A smartphone photograph of a skin lesion; a male patient aged 61; by history, prior skin cancer (patient or family); the patient was assessed as Fitzpatrick phototype III: 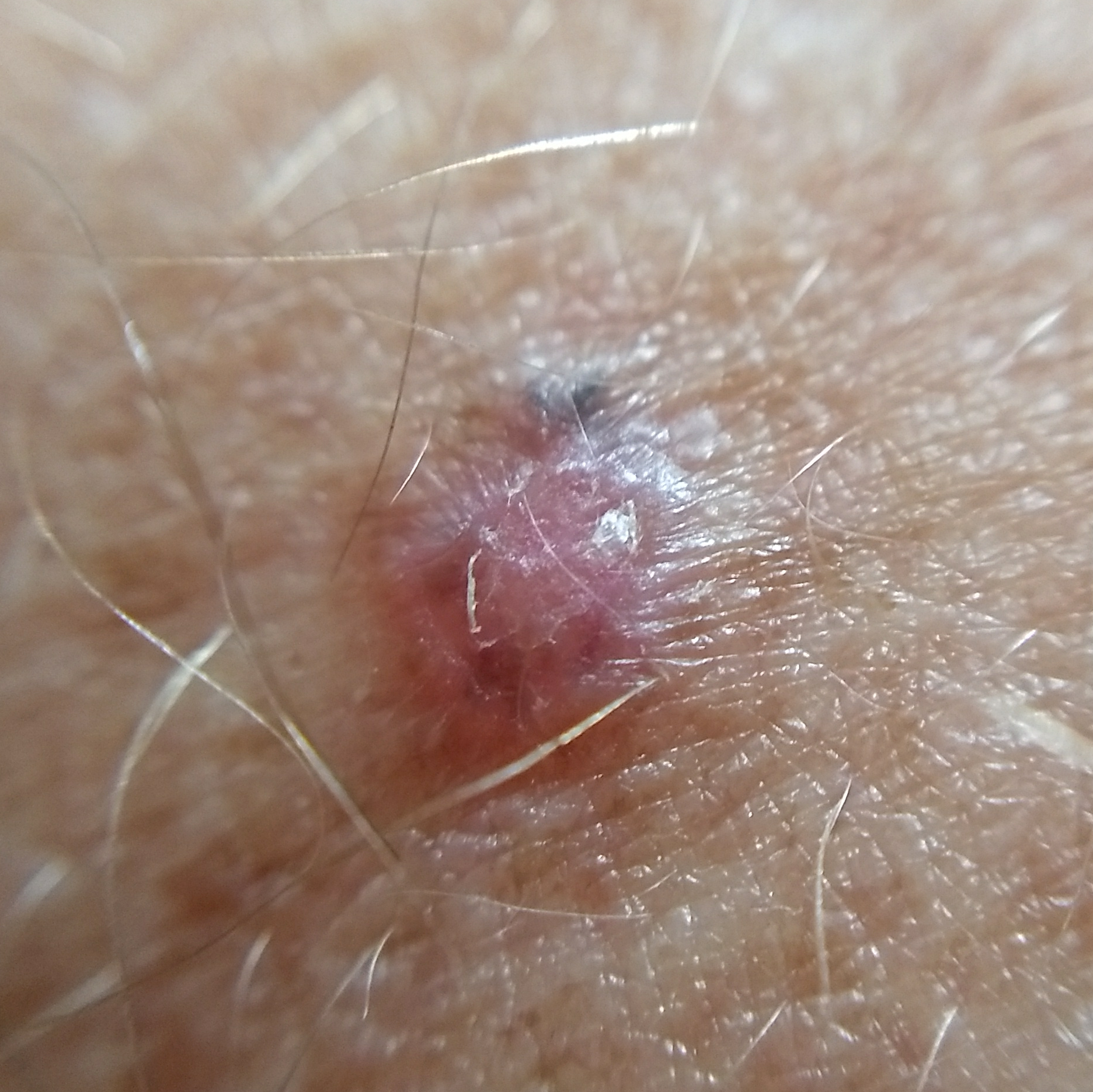| key | value |
|---|---|
| site | a forearm |
| lesion size | approx. 2 × 2 mm |
| reported symptoms | itching, elevation / no change in appearance |
| diagnostic label | basal cell carcinoma (biopsy-proven) |